A close-up photograph:
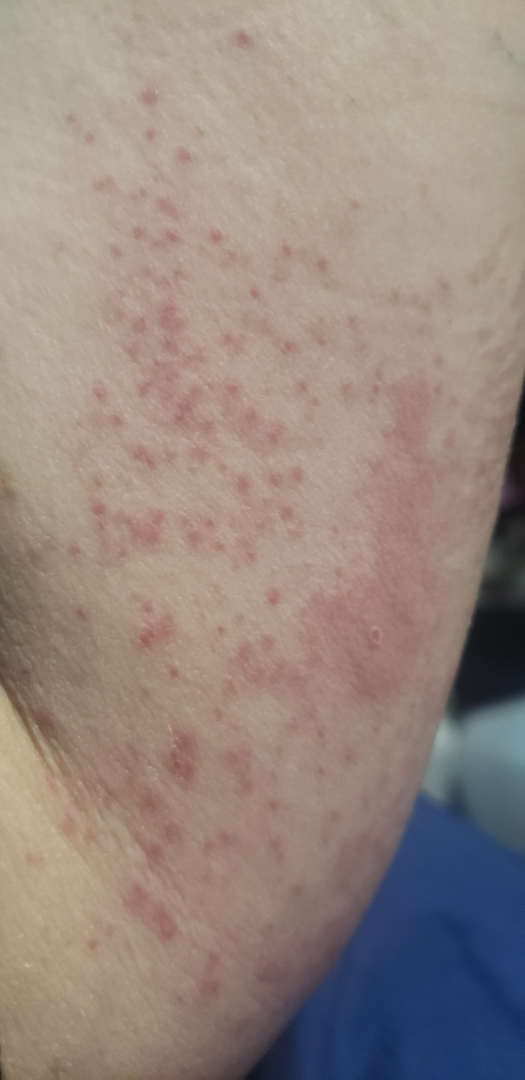Assessment: On remote dermatologist review, favoring Allergic Contact Dermatitis; possibly Hypersensitivity; the differential also includes Eczema.